Fitzpatrick phototype II. A male patient in their mid-40s.
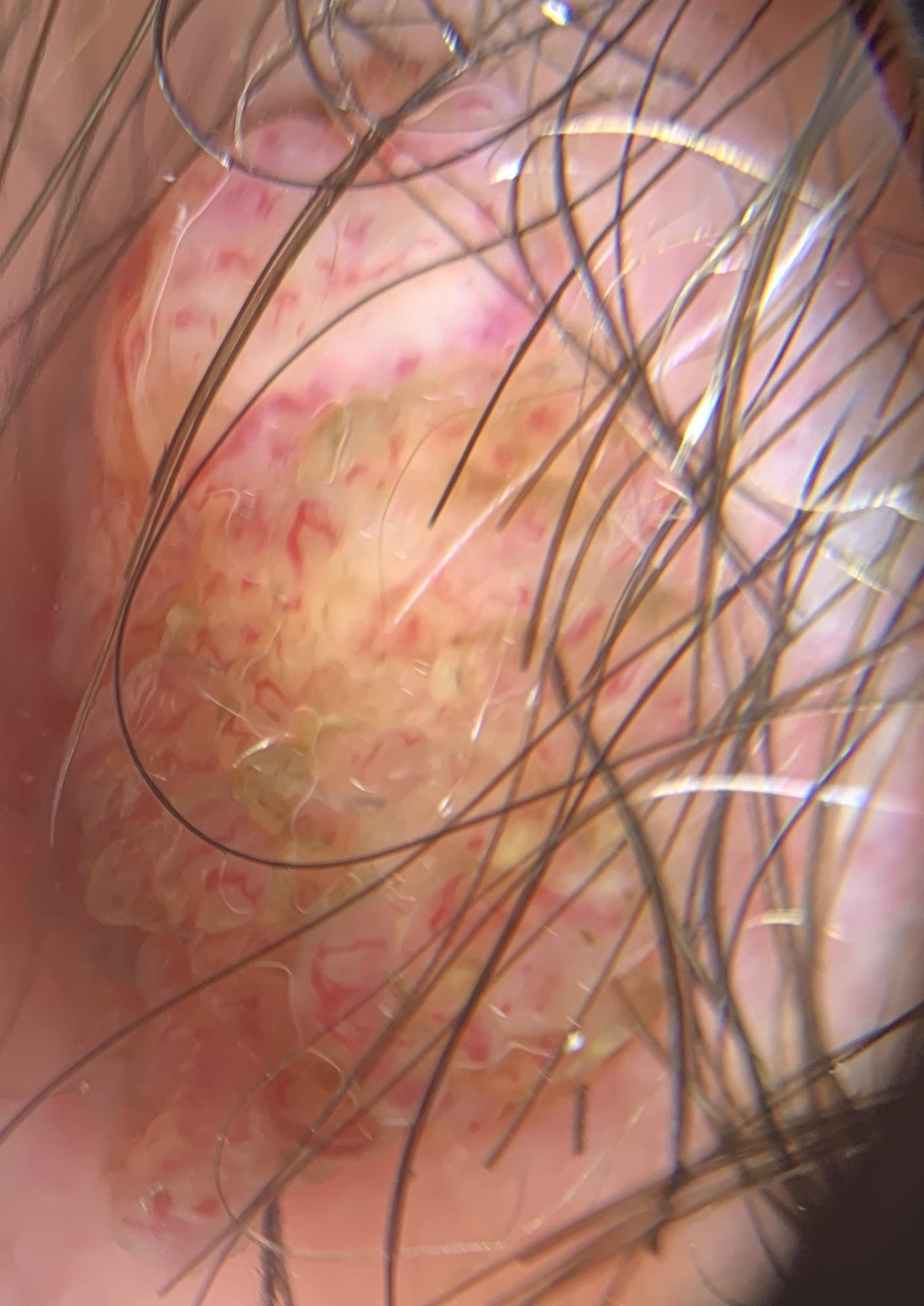The lesion is on the head or neck.
The clinical assessment was a nevus.